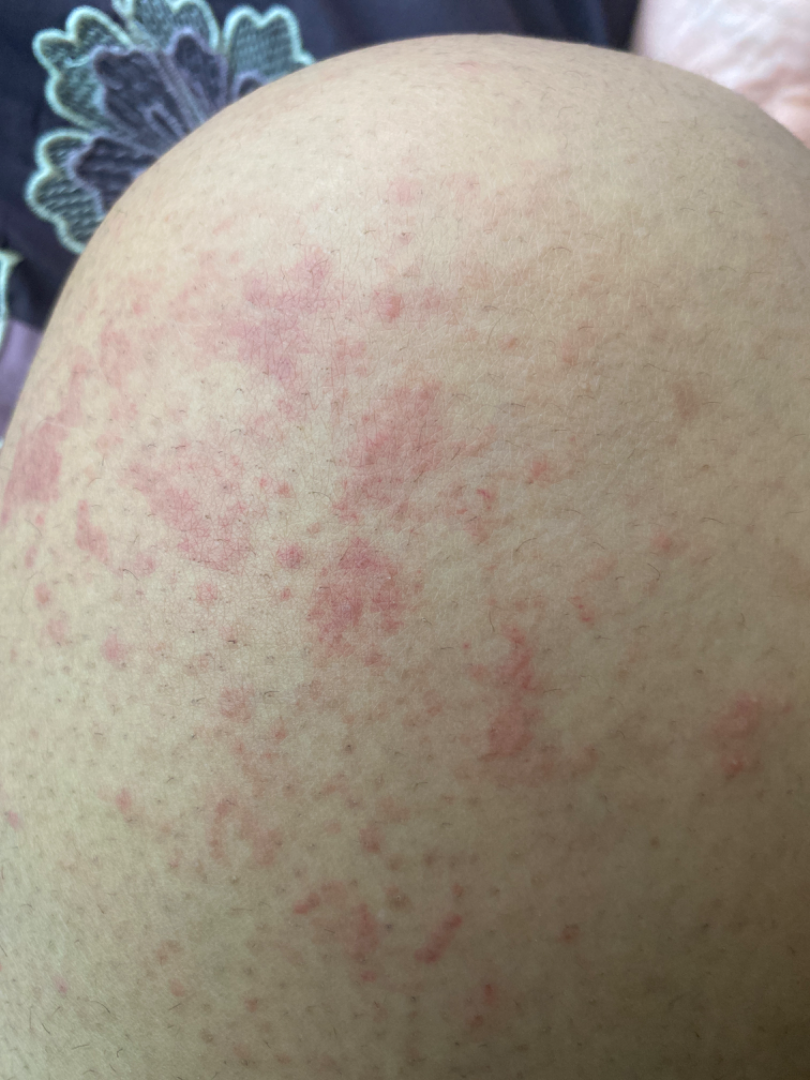Fitzpatrick II.
A close-up photograph.
The leg is involved.
Reported lesion symptoms include itching and bothersome appearance.
A single dermatologist reviewed the case: Allergic Contact Dermatitis and Irritant Contact Dermatitis were considered with similar weight.